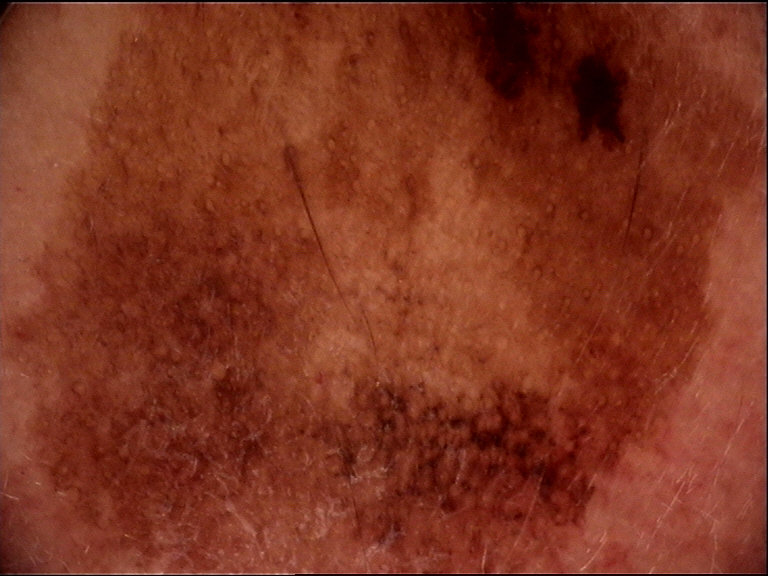Summary:
A skin lesion imaged with a dermatoscope.
Conclusion:
Confirmed on histopathology as a lentigo maligna.